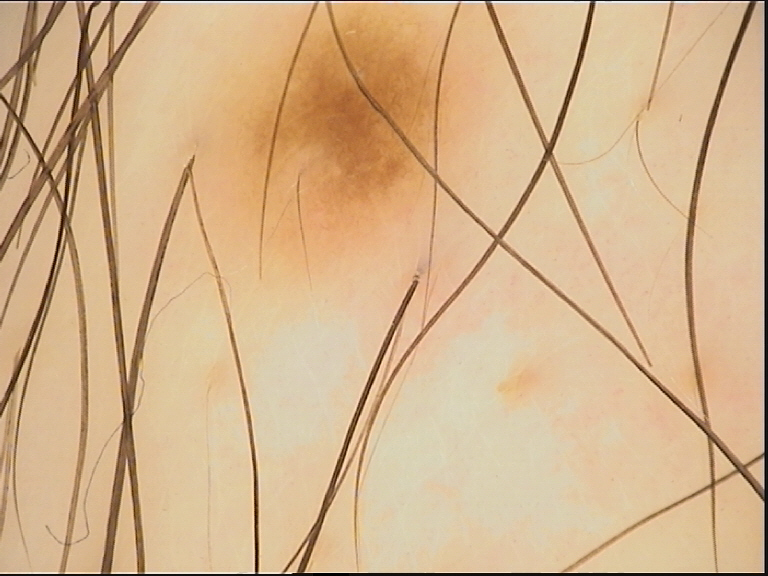A dermoscopic close-up of a skin lesion. This is a banal lesion. Labeled as a junctional nevus.